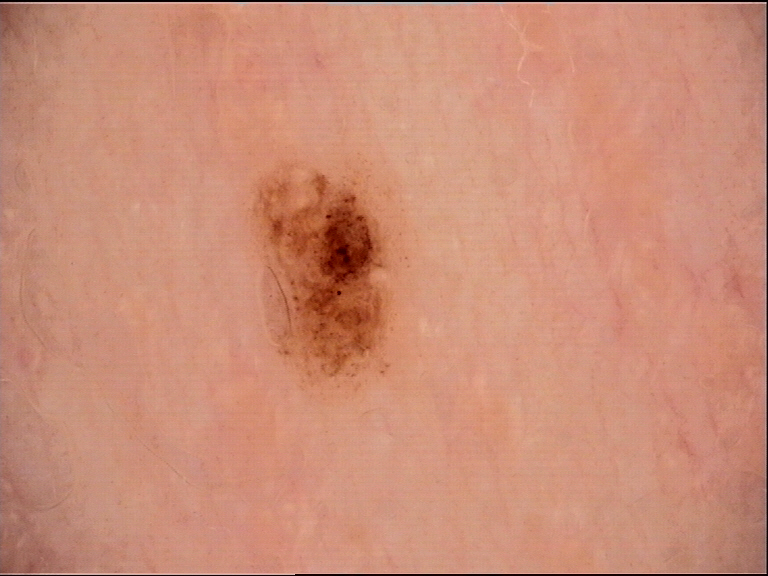Classified as a compound nevus.